A skin lesion imaged with a dermatoscope.
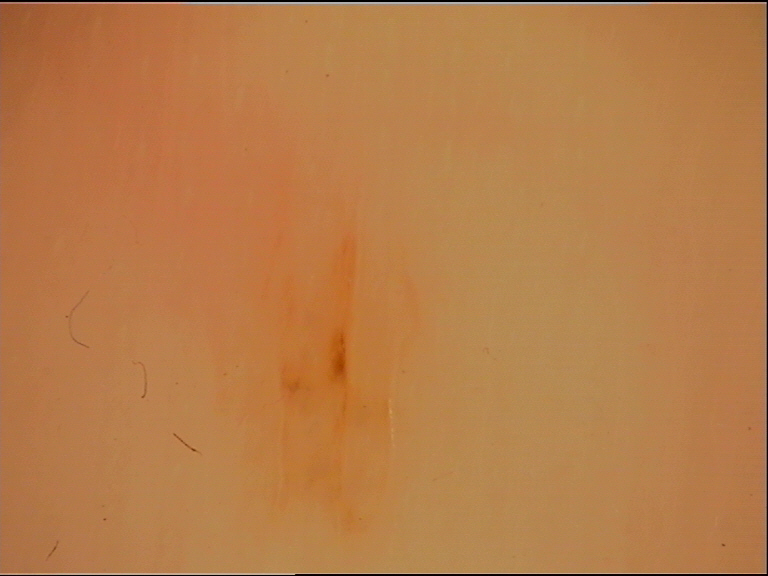This is a banal lesion. The diagnosis was an acral junctional nevus.